Skin tone: lay reviewers estimated 3 on the MST, an image taken at a distance.
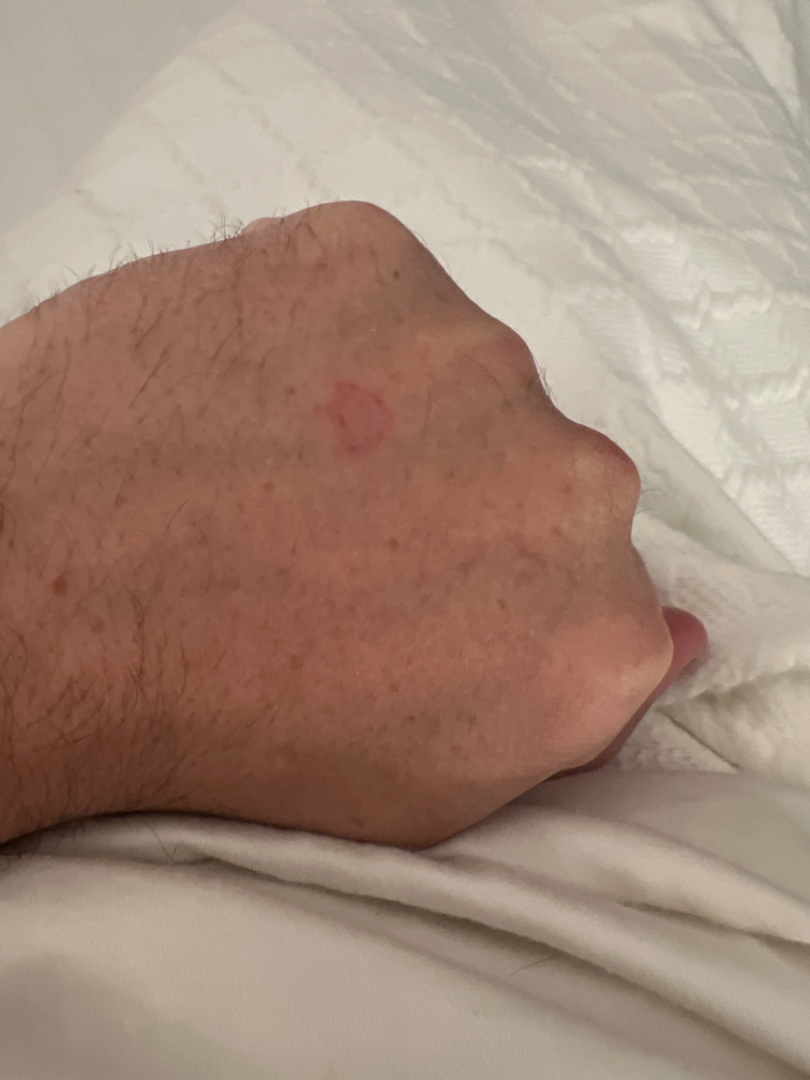  differential: Eczema